The patient notes the condition has been present for less than one week · the lesion is described as raised or bumpy · the lesion is associated with itching · self-categorized by the patient as a rash · a close-up photograph · the lesion involves the head or neck, back of the torso and front of the torso.
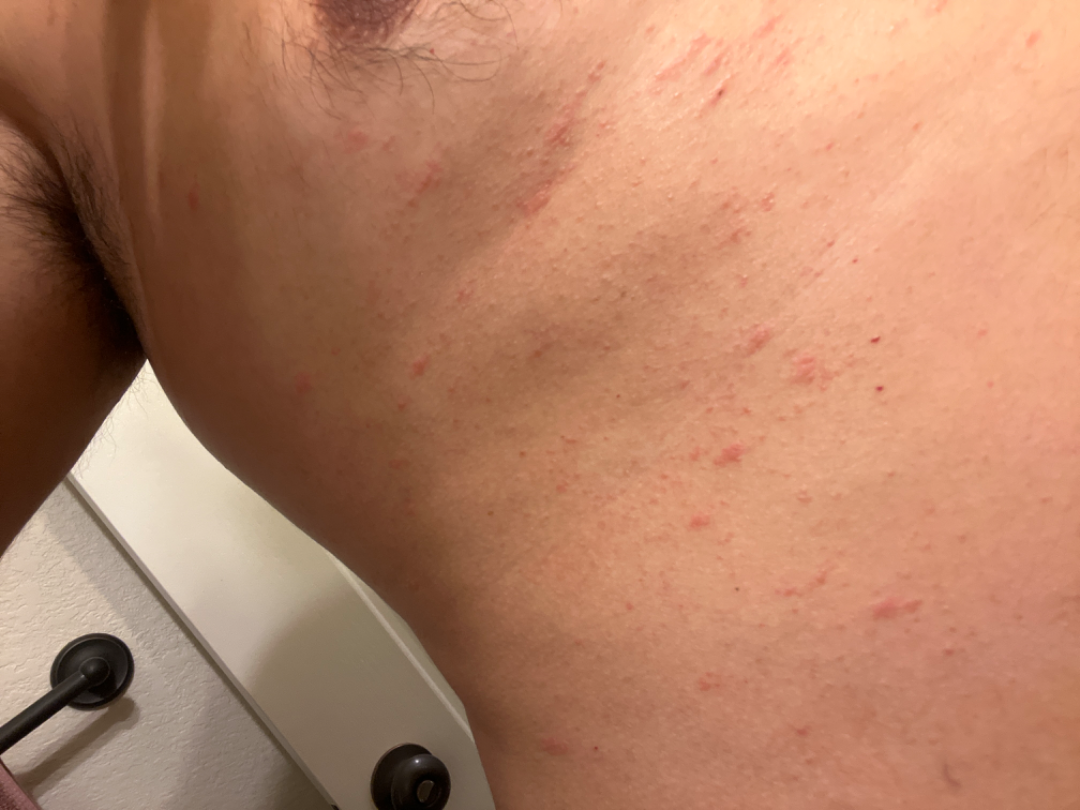Q: What is the differential diagnosis?
A: the differential is split between Acute dermatitis and Itchy skin eruption